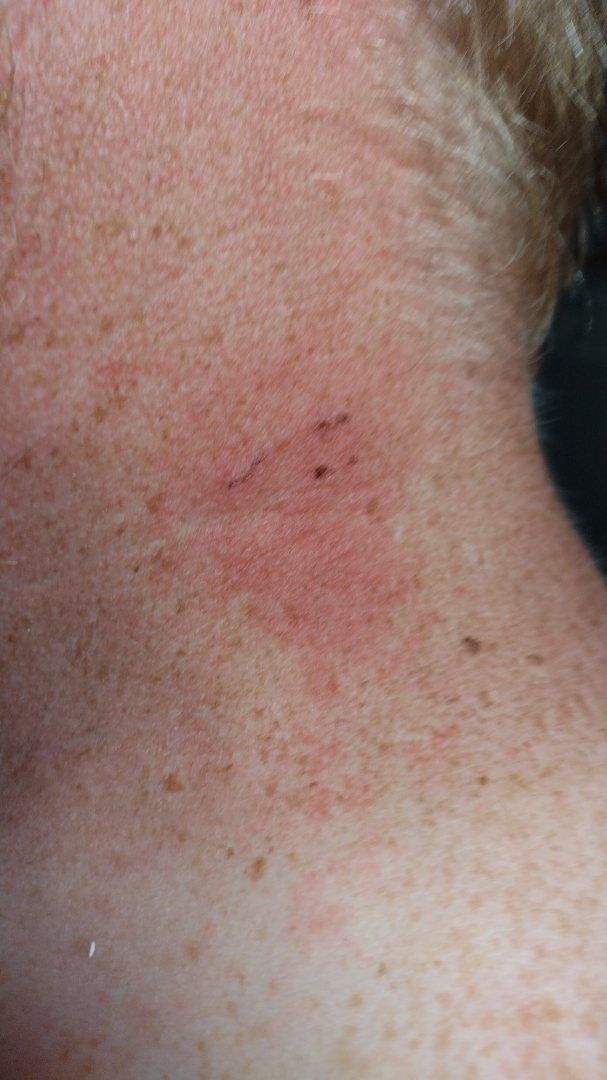On remote review of the image, favoring Allergic Contact Dermatitis; the differential also includes Eczema.